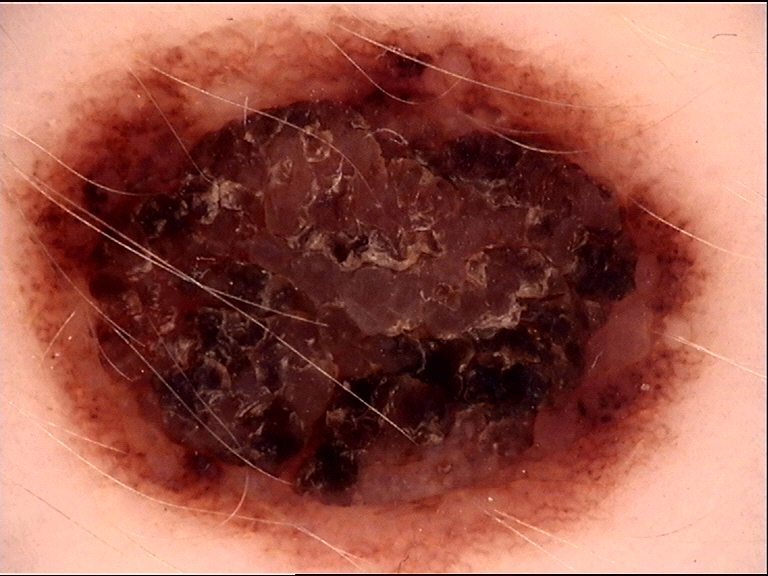Findings:
– diagnostic label: congenital dysplastic compound nevus (expert consensus)